A clinical photograph of a skin lesion; acquired for a research image collection, with no referral diagnosis; the patient describes having numerous moles; the patient reports a history of sunbed use: 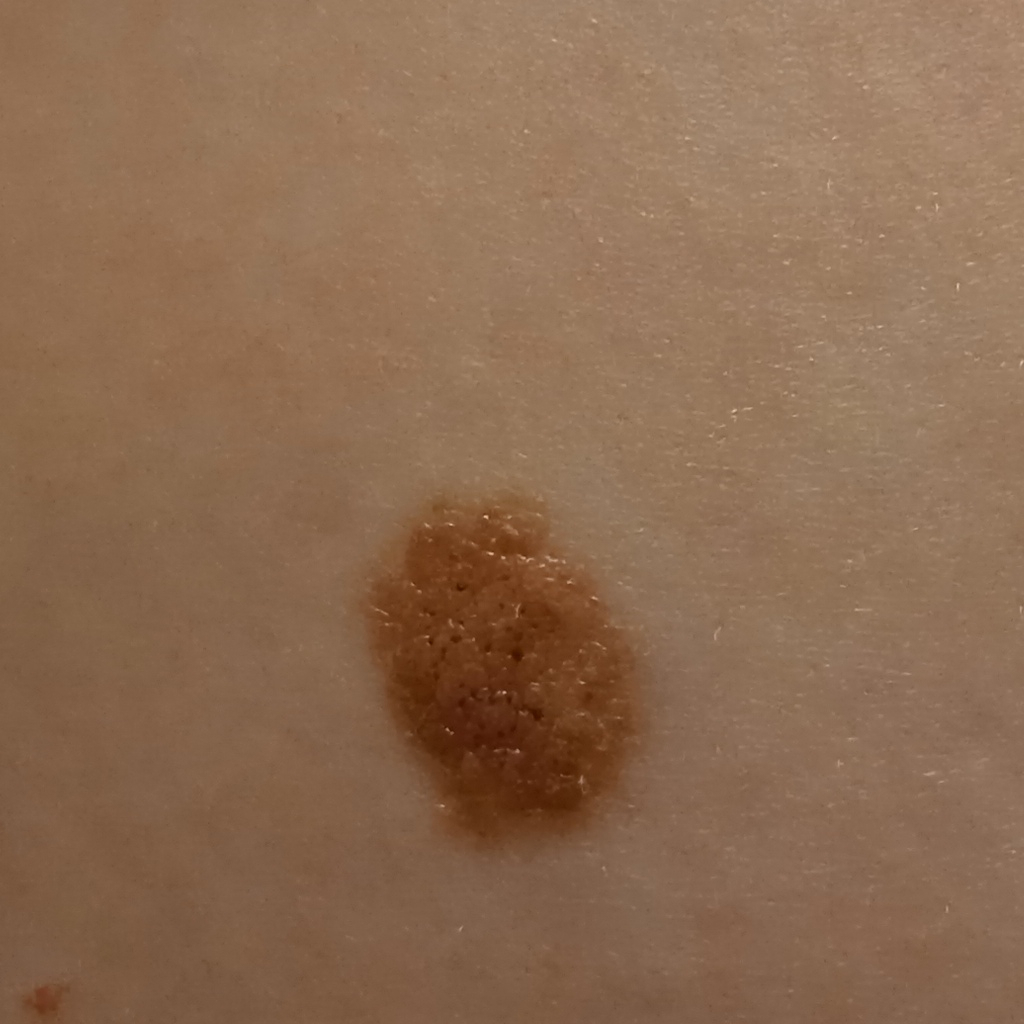Q: What is the anatomic site?
A: the torso
Q: Lesion size?
A: 13 mm
Q: What was the diagnosis?
A: melanocytic nevus (dermatologist consensus)